Located on the arm, the photograph is a close-up of the affected area, the subject is a male aged 18–29.
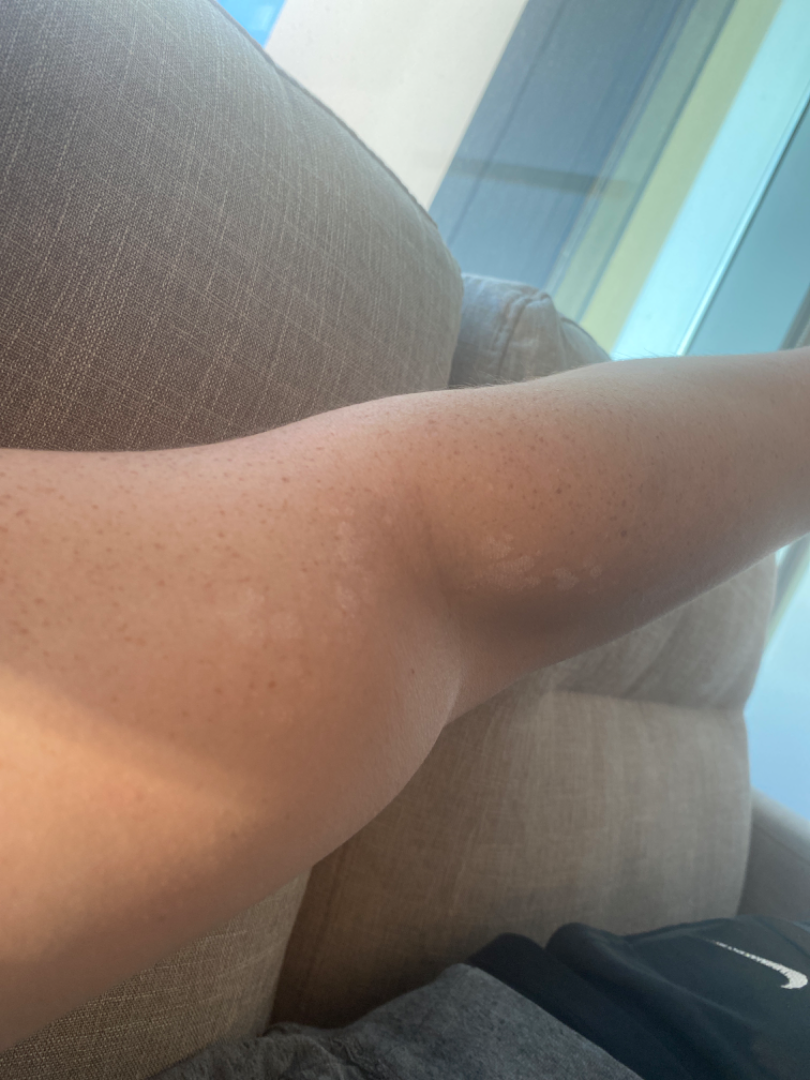Tinea Versicolor (weight 1.00).